This is a dermoscopic photograph of a skin lesion; the patient is a female in their mid- to late 60s.
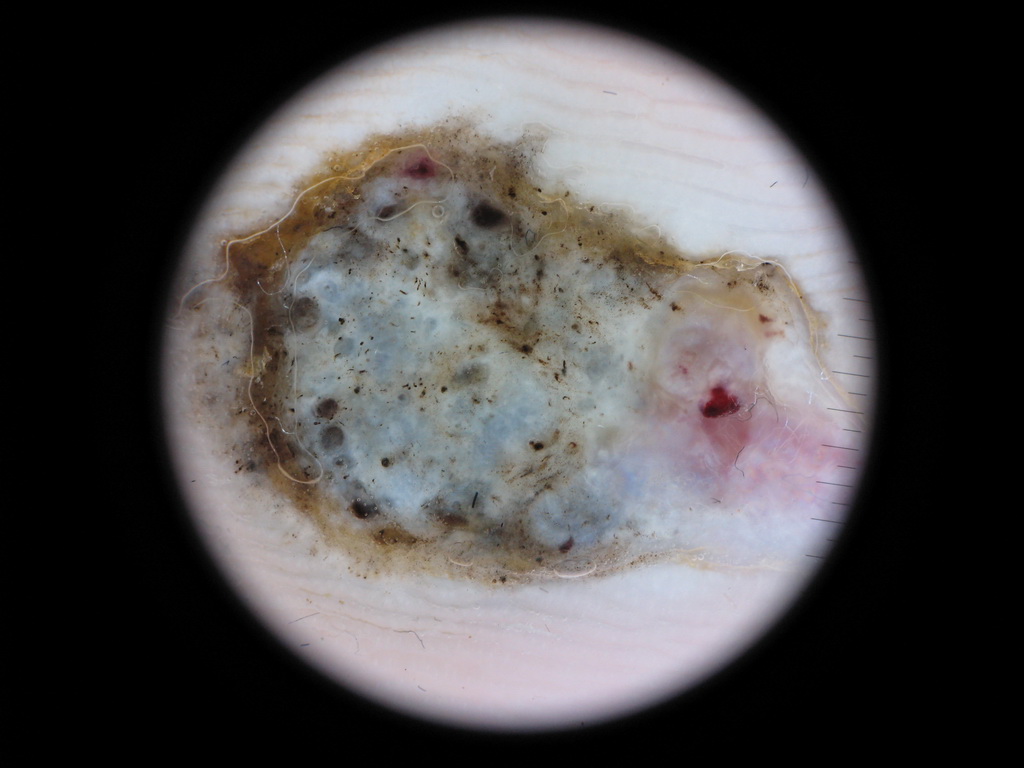With coordinates (x1, y1, x2, y2), the lesion's extent is (163, 111, 866, 593). The dermoscopic pattern shows no milia-like cysts, streaks, negative network, globules, or pigment network. Histopathologically confirmed as a melanoma.